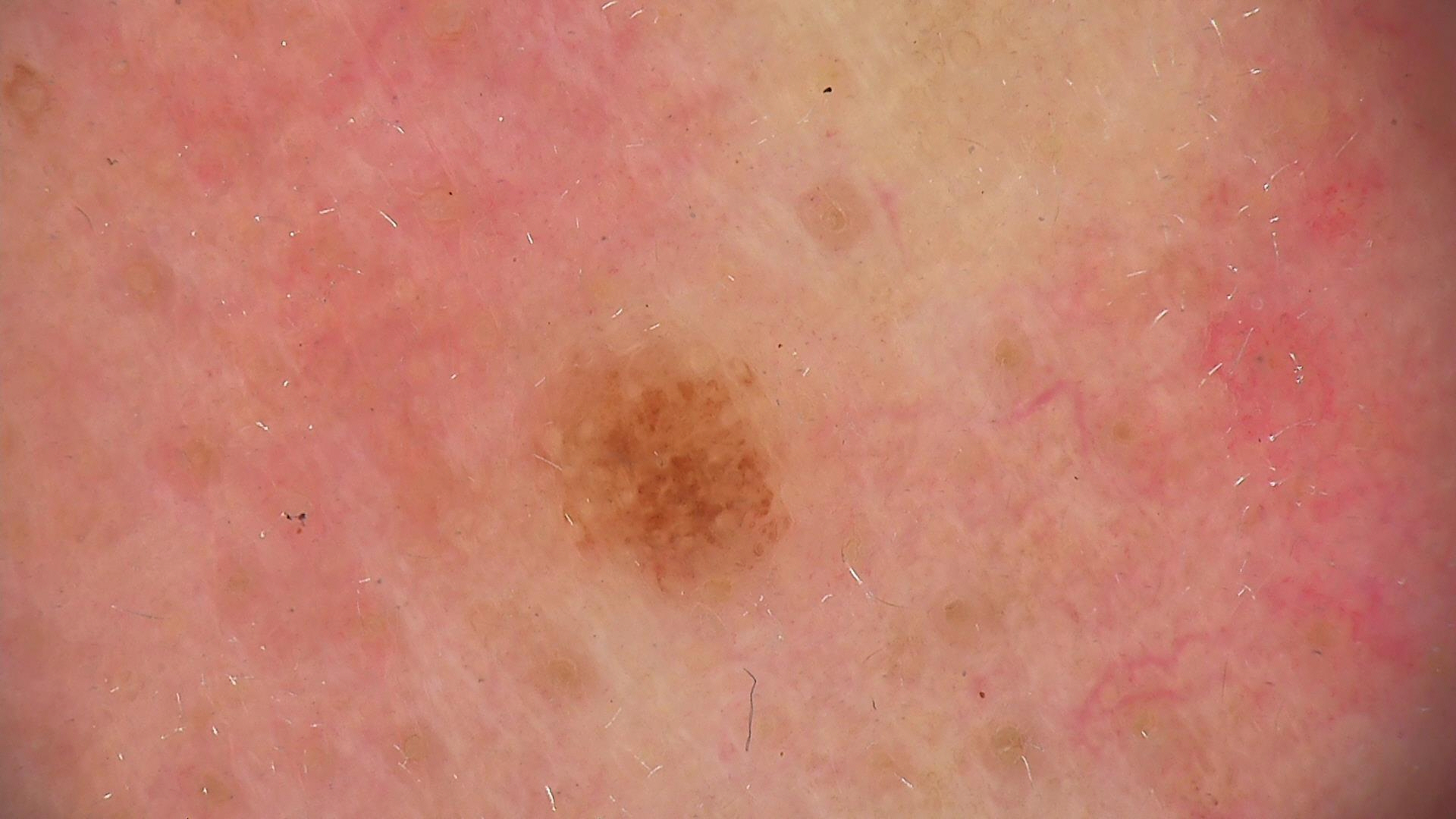  image: dermatoscopy
  diagnosis:
    name: Miescher nevus
    code: mcb
    malignancy: benign
    super_class: melanocytic
    confirmation: expert consensus